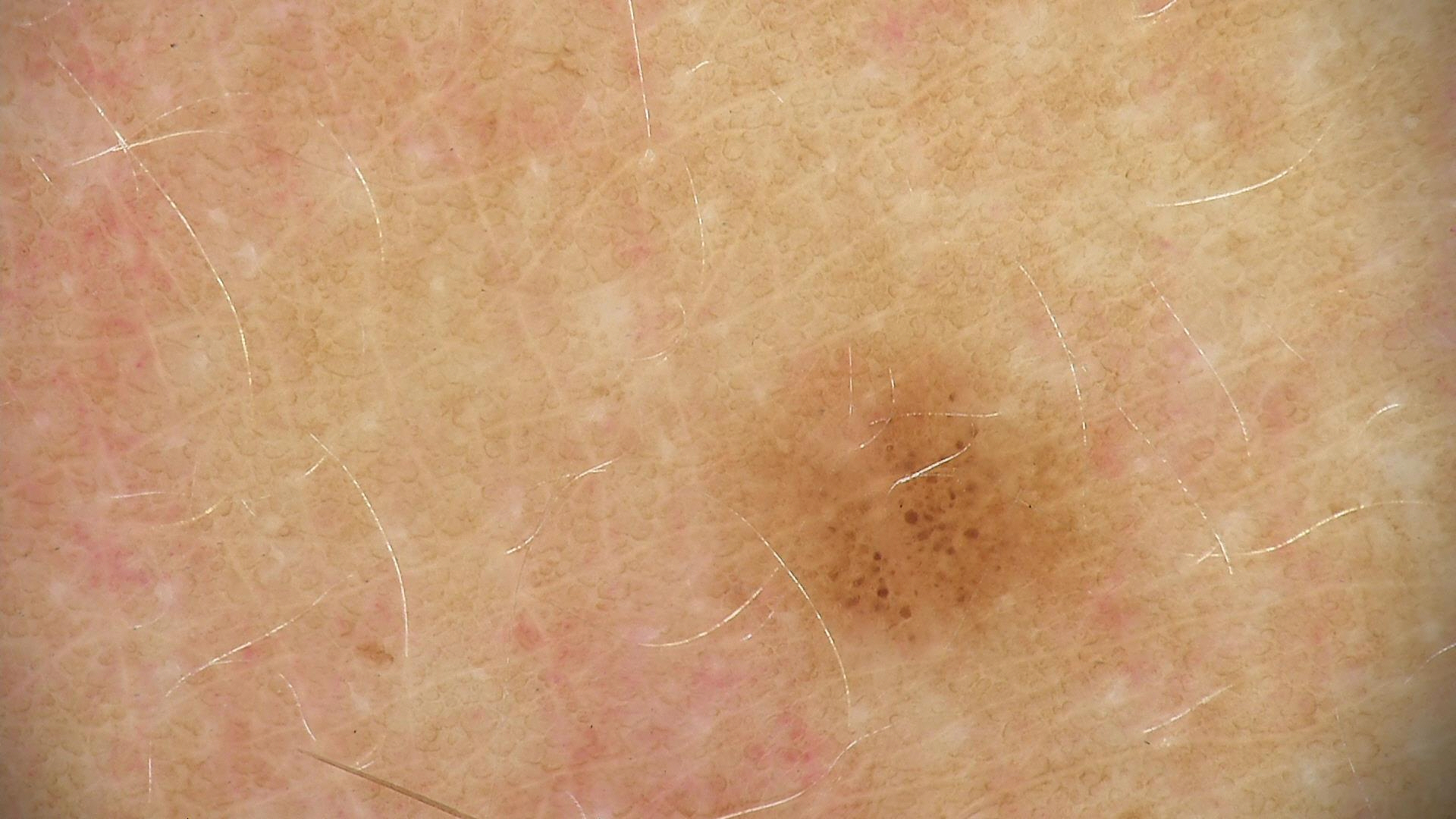Diagnosed as a benign lesion — a dysplastic junctional nevus.